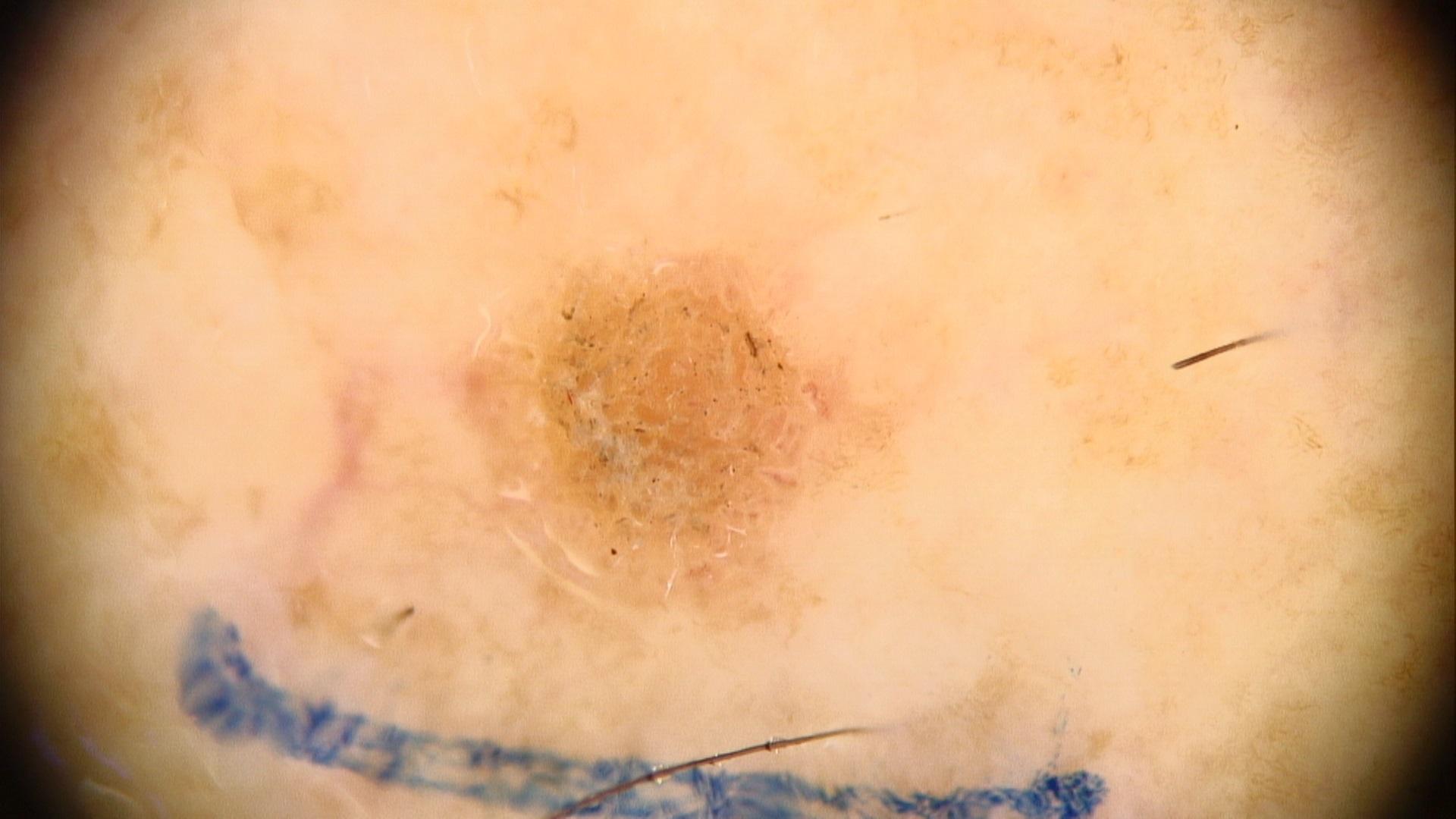Q: What does the history note?
A: a prior melanoma
Q: What are the patient's age and sex?
A: female, about 65 years old
Q: How was this image acquired?
A: dermatoscopic image
Q: Where is the lesion located?
A: a lower extremity
Q: What is the diagnosis?
A: Solar or actinic keratosis (biopsy-proven)